A patient in their 40s. A clinical photograph showing a skin lesion — 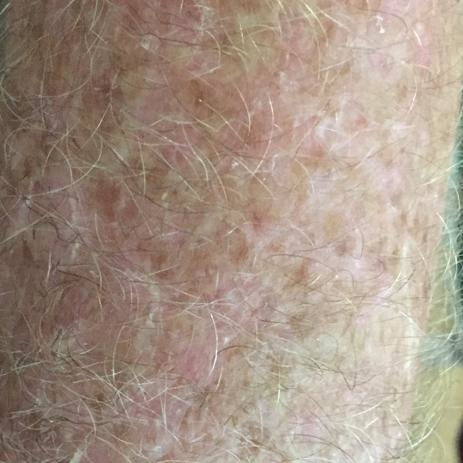The lesion is on an arm.
The patient reports that the lesion itches.
The clinical impression was an actinic keratosis.